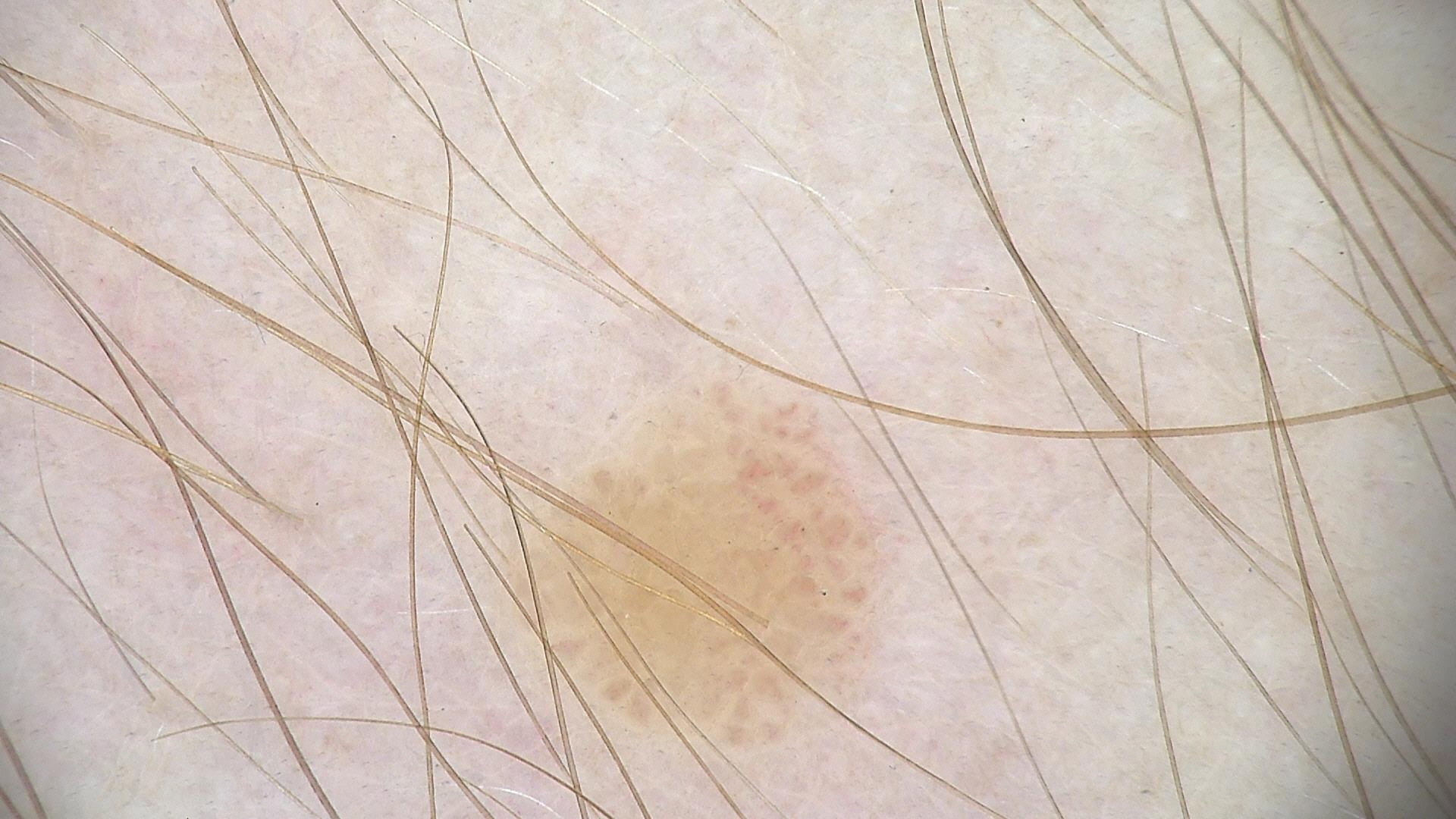Diagnosed as a dysplastic junctional nevus.